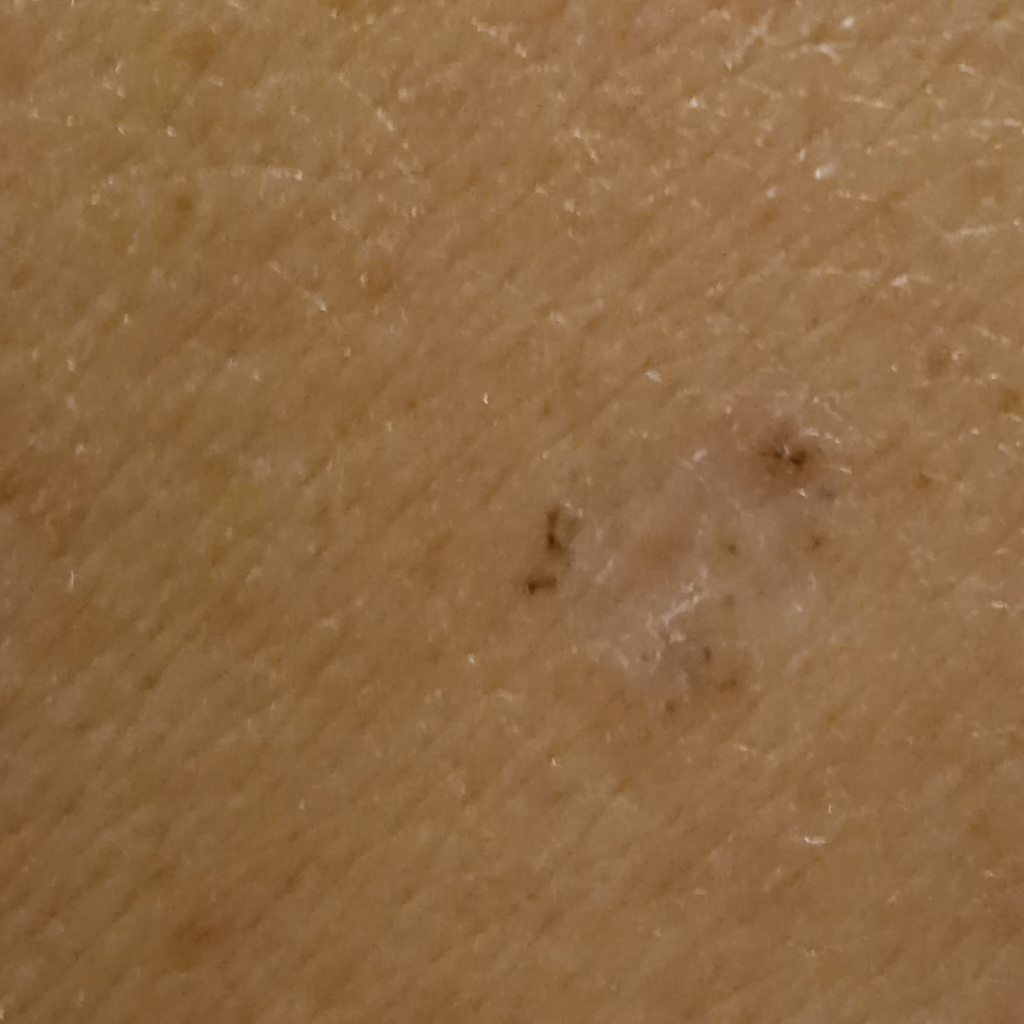- nevus count · few melanocytic nevi overall
- clinical context · clinical suspicion of basal cell carcinoma
- patient · female, 60 years of age
- sun reaction · skin tans without first burning
- image type · clinical photo
- risk factors · a personal history of skin cancer, a personal history of cancer
- body site · the back
- diameter · 7.8 mm
- diagnosis · basal cell carcinoma (dermatologist consensus)